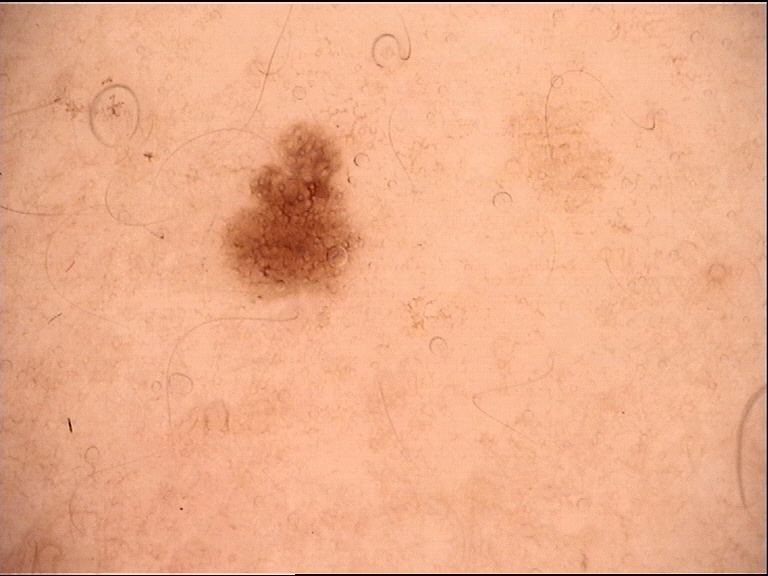Case:
A dermoscopic close-up of a skin lesion.
Impression:
The diagnostic label was a dysplastic junctional nevus.